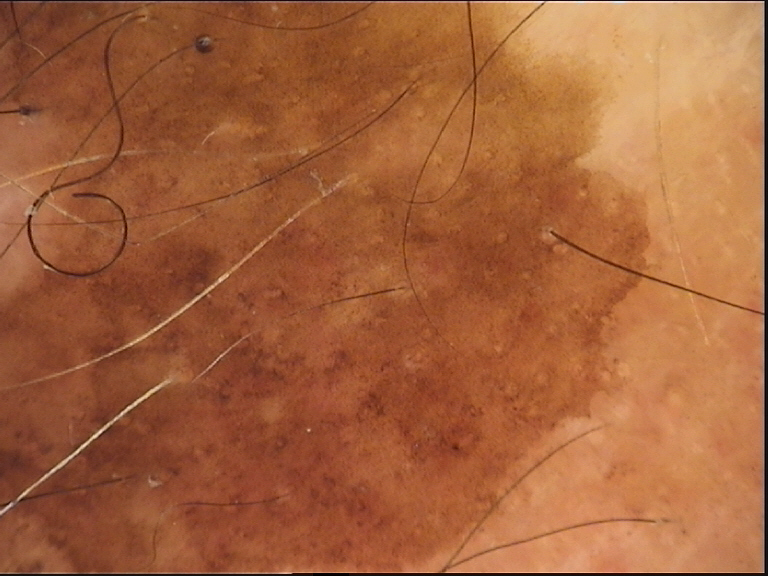Q: What kind of image is this?
A: dermatoscopy
Q: What is this lesion?
A: seborrheic keratosis (expert consensus)